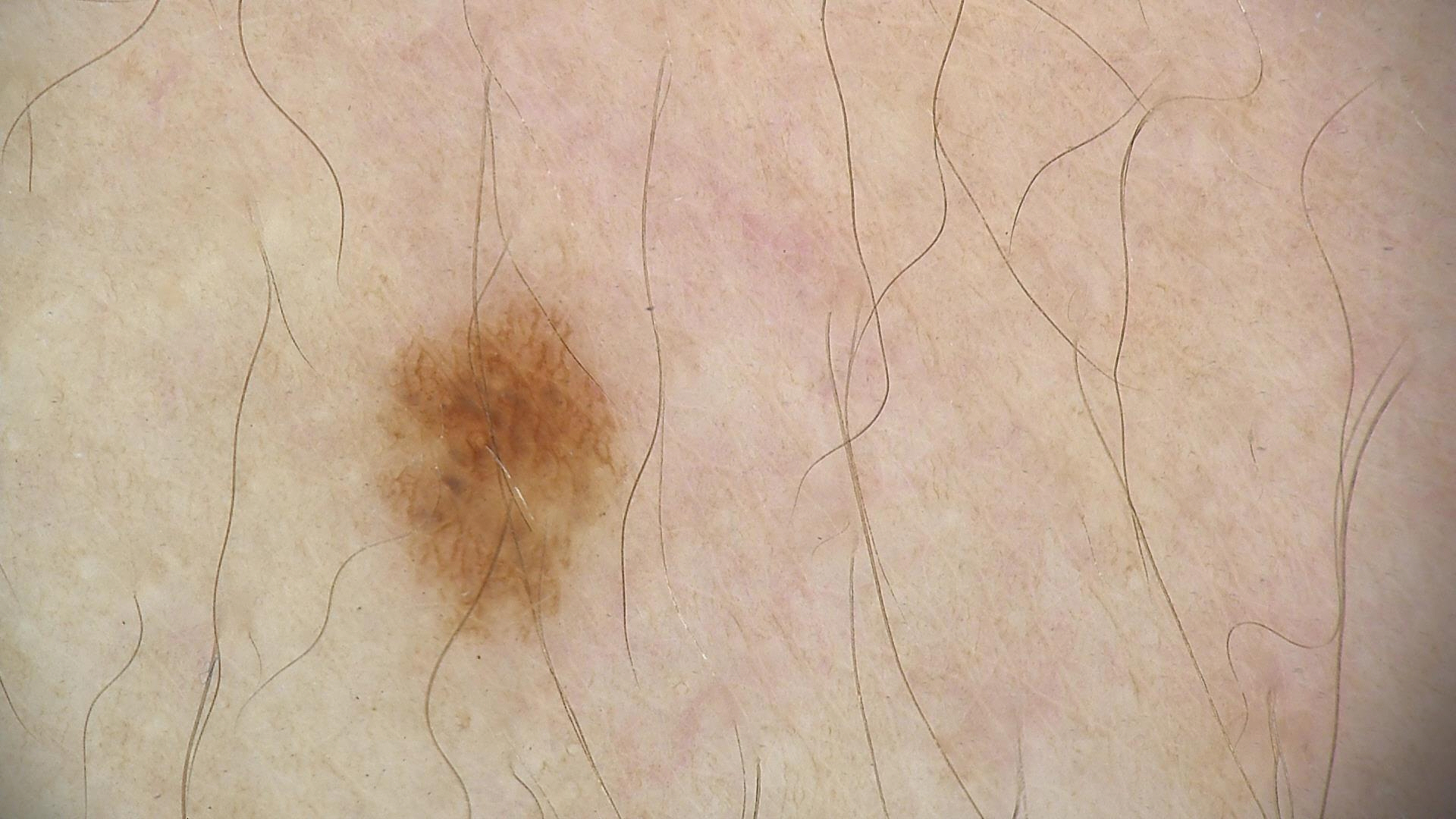Conclusion: Classified as a dysplastic junctional nevus.